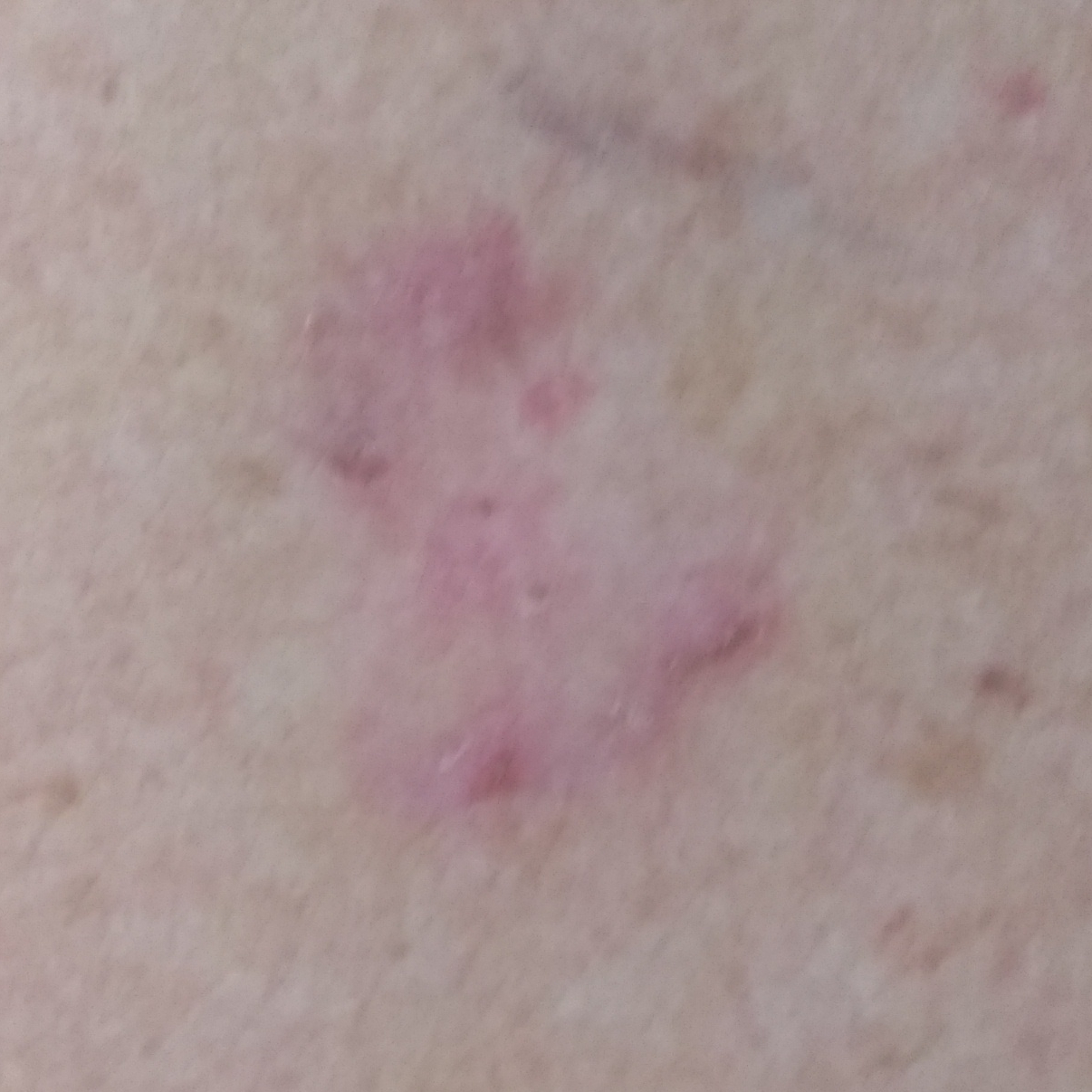image type: smartphone clinical photo
patient: female, 53 years old
anatomic site: the chest
reported symptoms: no elevation
diagnostic label: basal cell carcinoma (biopsy-proven)